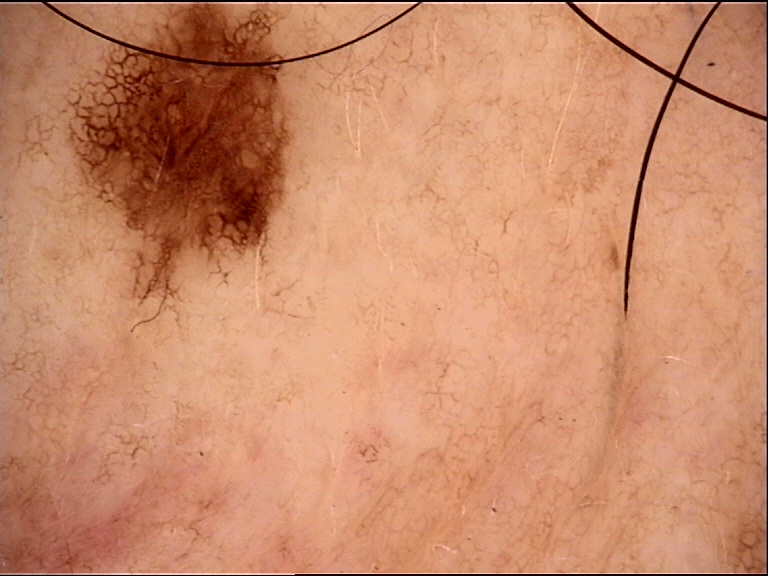Case: A dermatoscopic image of a skin lesion. Impression: The diagnostic label was a dysplastic junctional nevus.